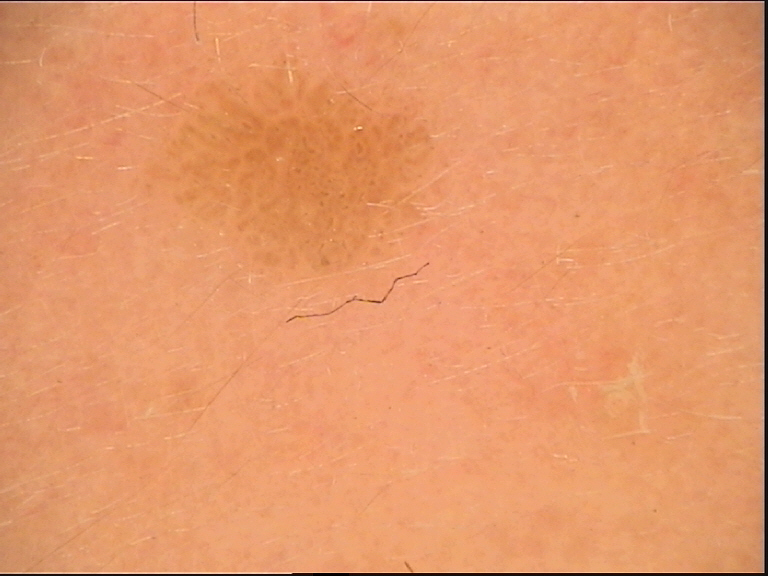{"lesion_type": {"main_class": "keratinocytic"}, "diagnosis": {"name": "seborrheic keratosis", "code": "sk", "malignancy": "benign", "super_class": "non-melanocytic", "confirmation": "expert consensus"}}